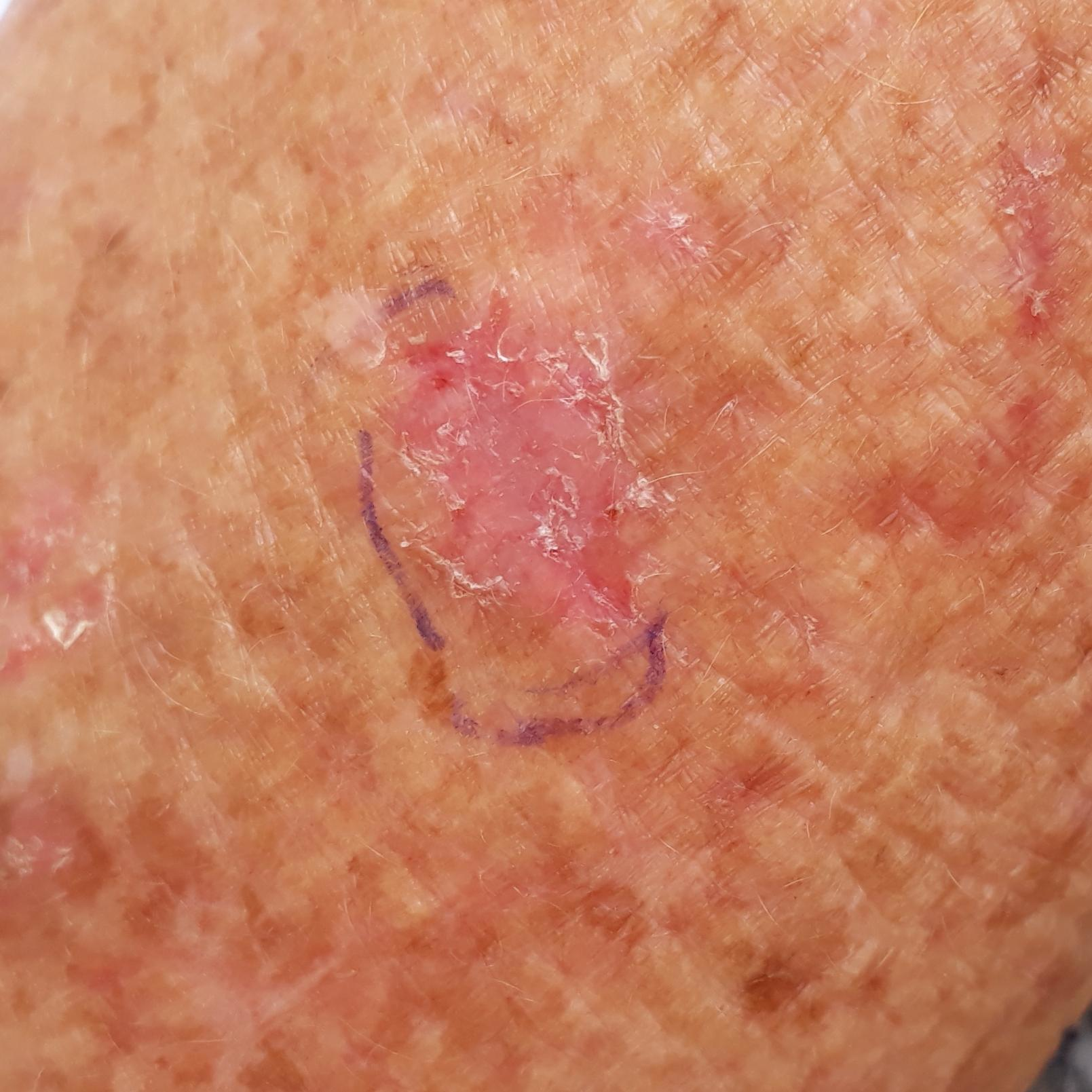<lesion>
  <patient>
    <age>65</age>
    <gender>female</gender>
  </patient>
  <symptoms>
    <present>itching</present>
  </symptoms>
  <diagnosis>
    <name>actinic keratosis</name>
    <code>ACK</code>
    <malignancy>indeterminate</malignancy>
    <confirmation>clinical consensus</confirmation>
  </diagnosis>
</lesion>